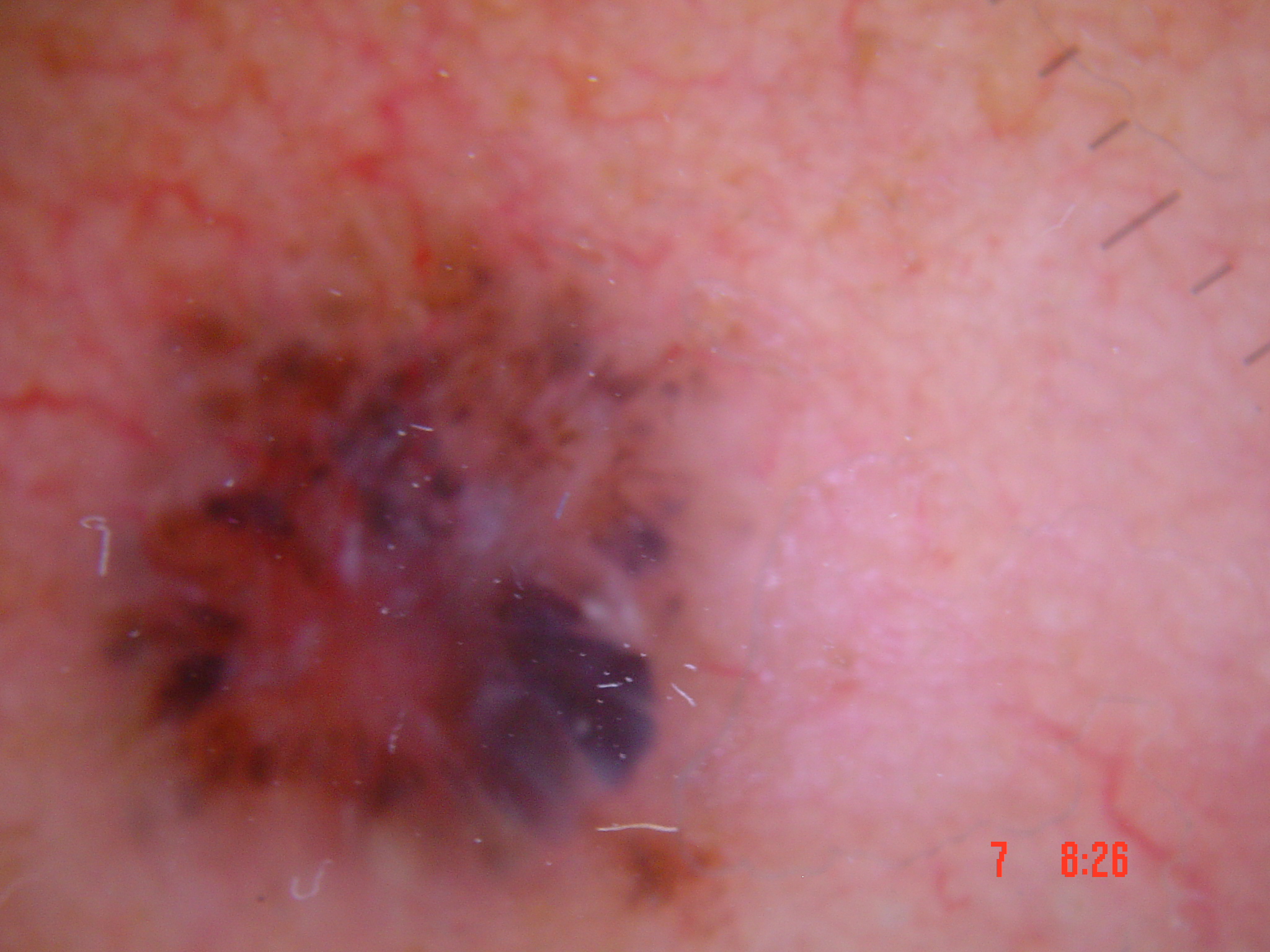| key | value |
|---|---|
| image type | dermoscopy |
| classification | keratinocytic |
| class | basal cell carcinoma (biopsy-proven) |